Dermoscopy of a skin lesion.
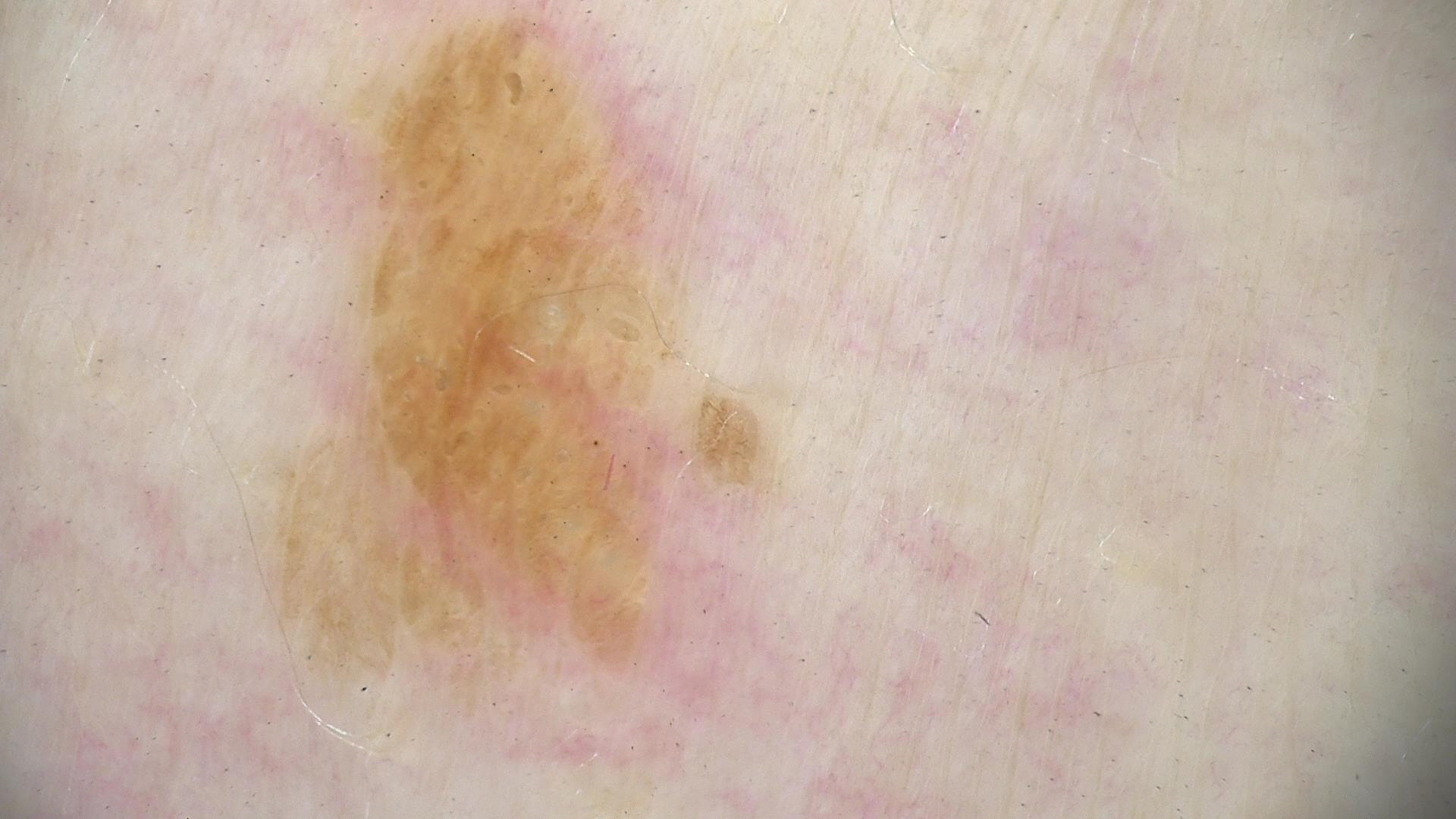Classified as a benign, keratinocytic lesion — a seborrheic keratosis.